A dermoscopic photograph of a skin lesion:
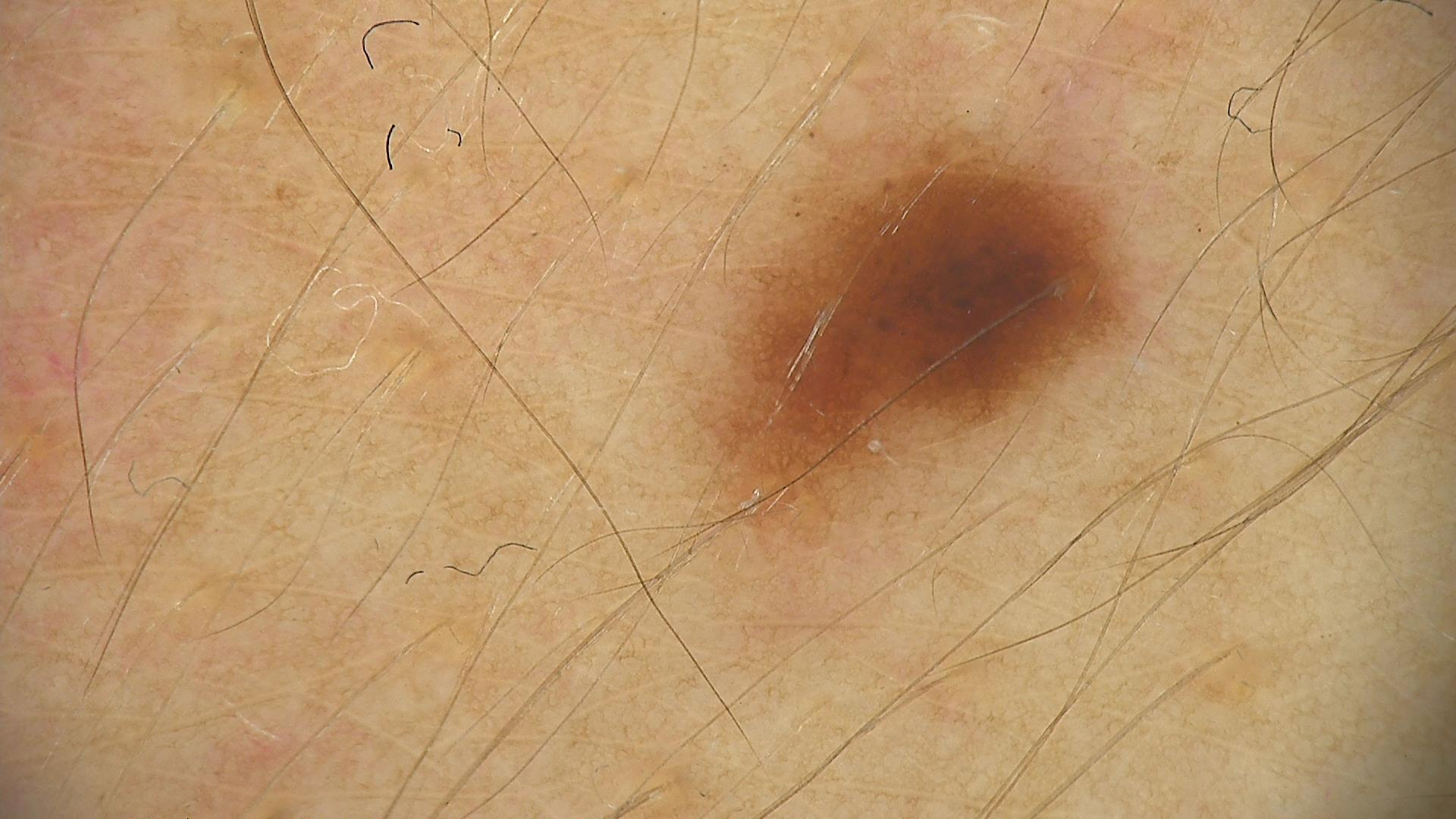Labeled as a dysplastic junctional nevus.